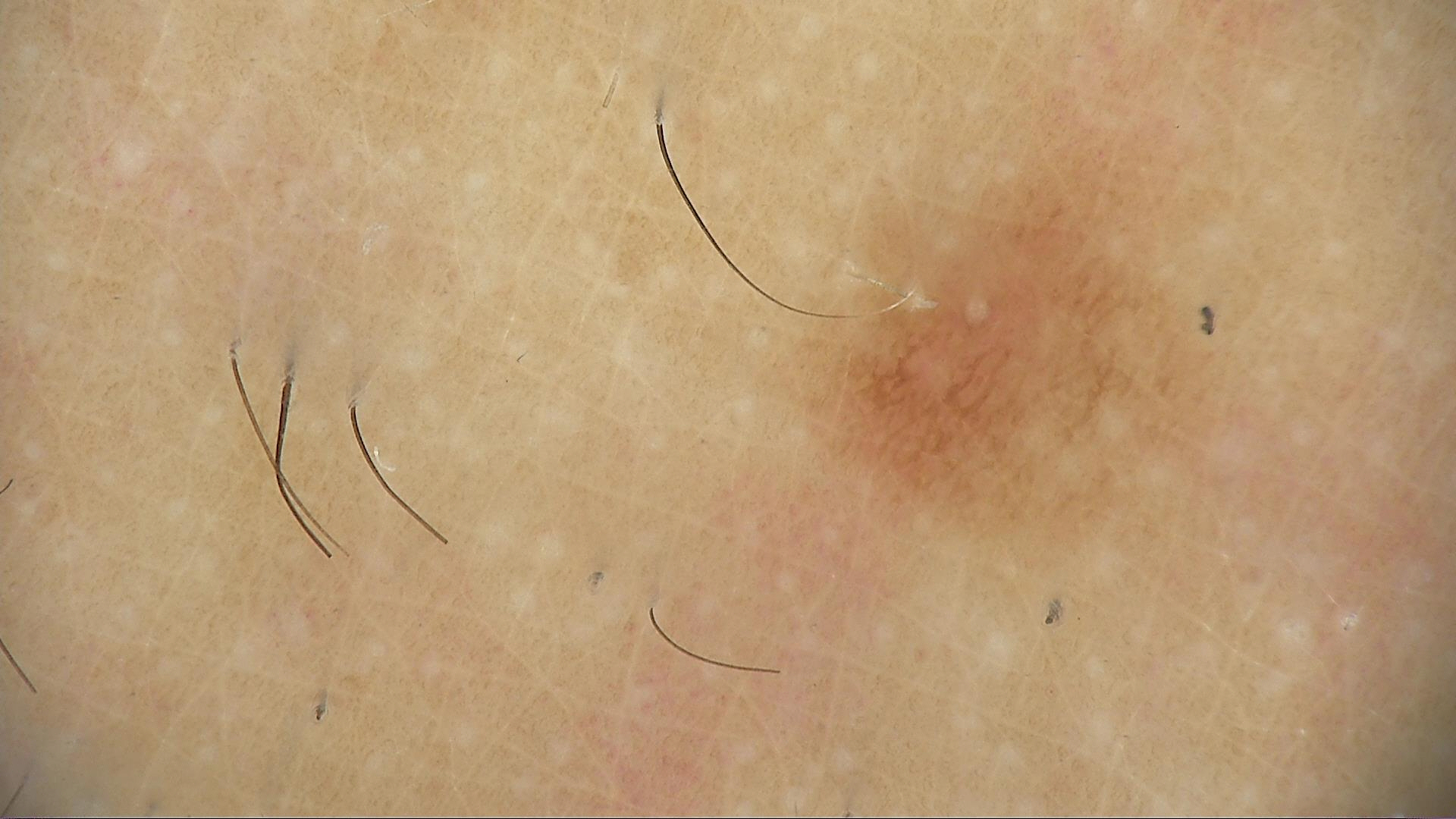A dermoscopic photograph of a skin lesion.
The diagnosis was a dysplastic junctional nevus.